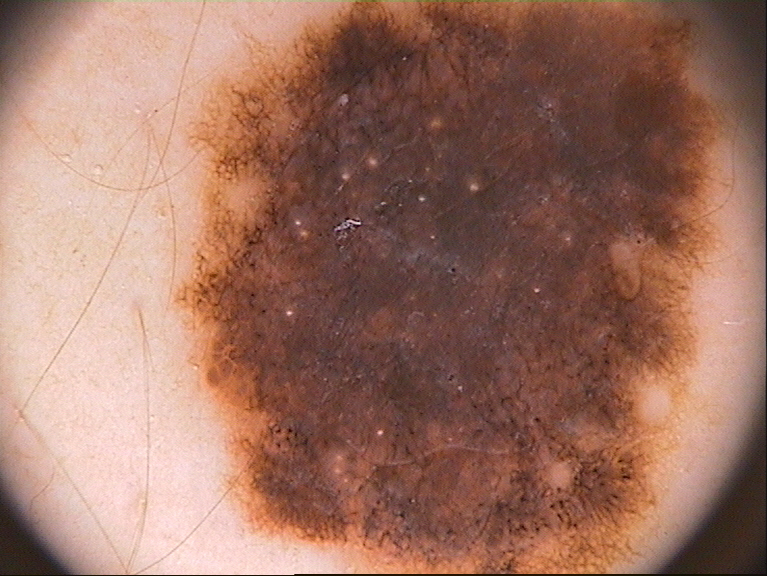{"image": {"modality": "dermoscopy"}, "lesion_location": {"bbox_xyxy": [172, 1, 742, 571]}, "lesion_extent": "large", "dermoscopic_features": {"present": ["globules", "pigment network"], "absent": ["negative network", "milia-like cysts", "streaks"]}, "diagnosis": {"name": "melanocytic nevus", "malignancy": "benign", "lineage": "melanocytic", "provenance": "clinical"}}